A dermoscopic image of a skin lesion:
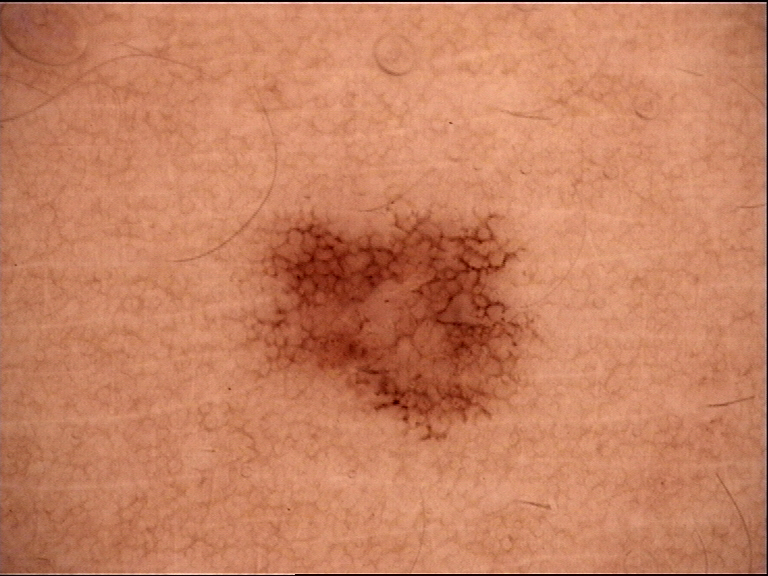<case>
<diagnosis>
<name>dysplastic junctional nevus</name>
<code>jd</code>
<malignancy>benign</malignancy>
<super_class>melanocytic</super_class>
<confirmation>expert consensus</confirmation>
</diagnosis>
</case>